A dermoscopic image of a skin lesion, a male patient aged approximately 30.
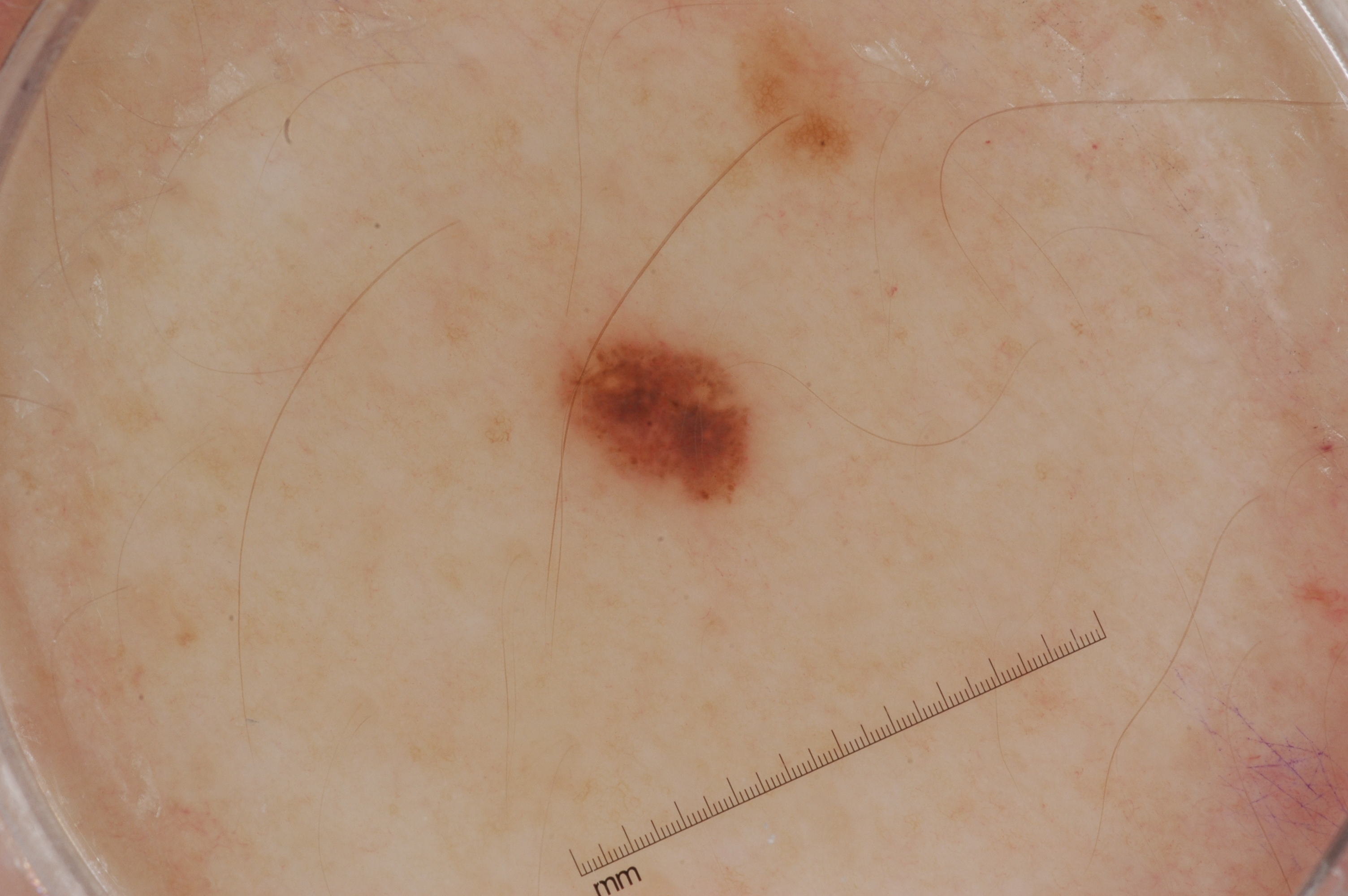Summary:
The lesion spans x1=548 y1=315 x2=758 y2=518. The lesion occupies roughly 3% of the field. Dermoscopic examination shows no negative network, pigment network, streaks, or milia-like cysts.
Impression:
The lesion was assessed as a melanocytic nevus.